A dermoscopy image of a single skin lesion: 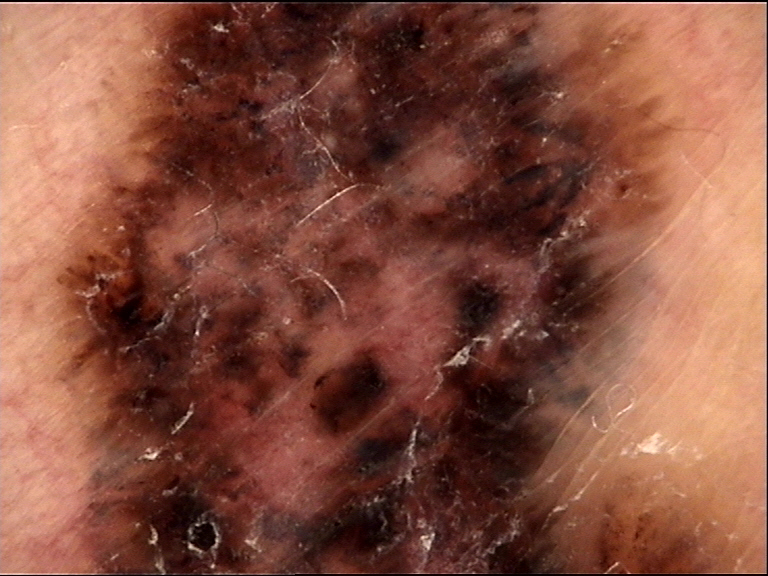Biopsy-confirmed as a skin cancer — a basal cell carcinoma.